This is a close-up image — 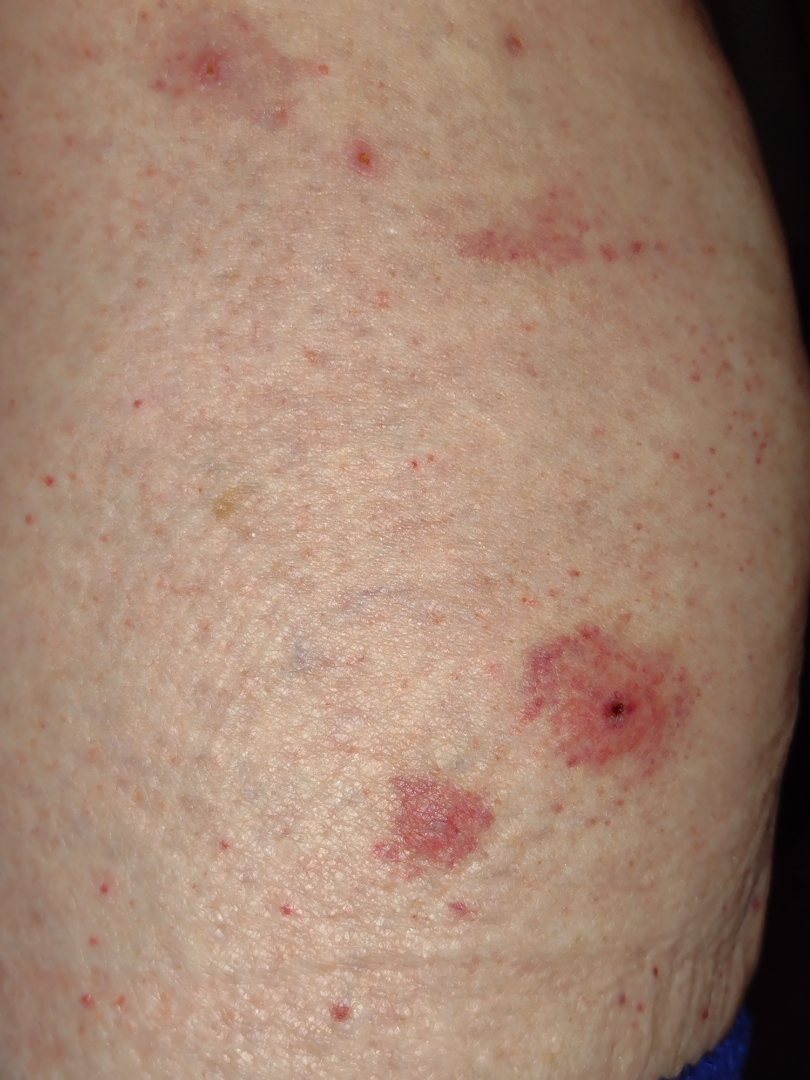Notes:
* differential diagnosis: Pigmented purpuric eruption (most likely); Purpura (possible)